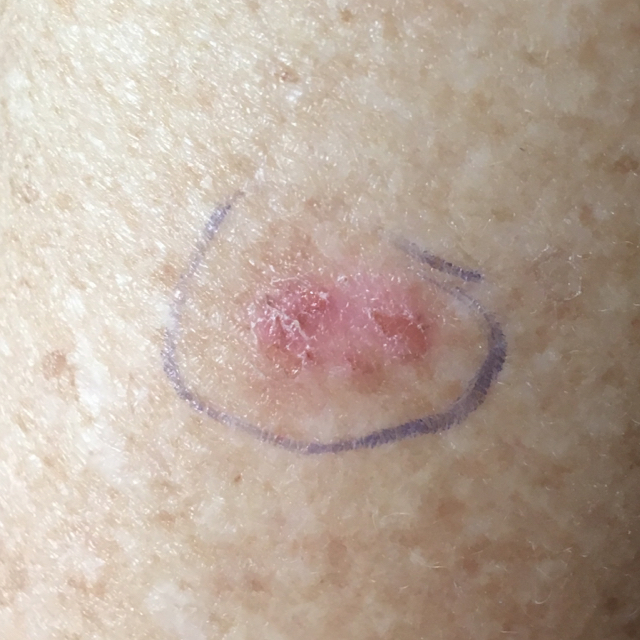Case:
• image type: smartphone clinical photo
• subject: 77 years old
• body site: a forearm
• impression: actinic keratosis (clinical consensus)